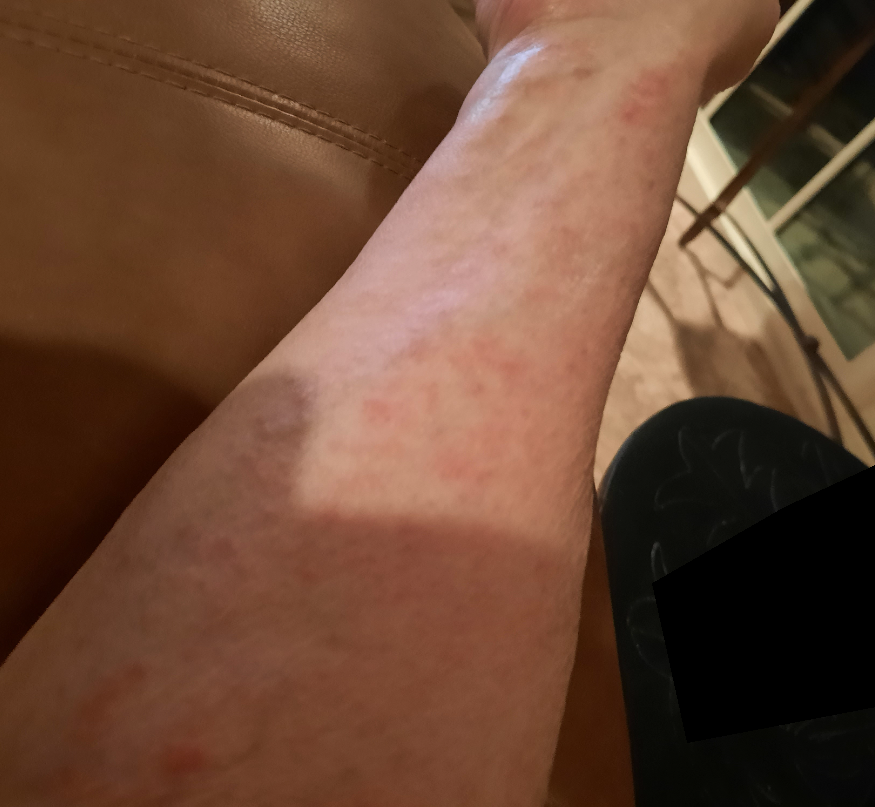assessment=indeterminate from the photograph